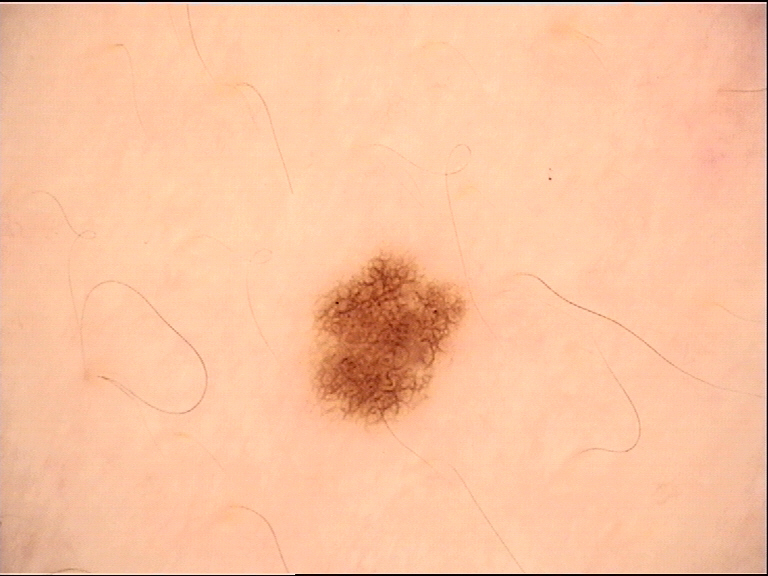assessment — dysplastic junctional nevus (expert consensus)